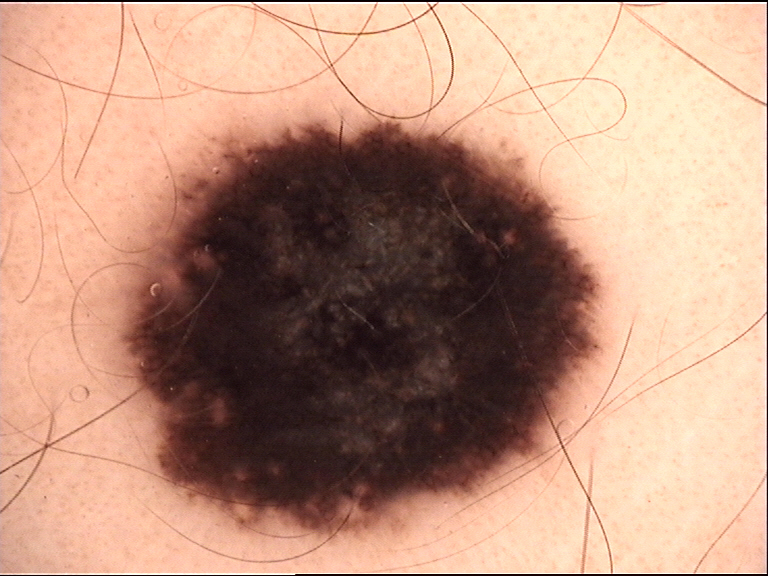<lesion>
<diagnosis>
<name>melanoma</name>
<code>mel</code>
<malignancy>malignant</malignancy>
<super_class>melanocytic</super_class>
<confirmation>histopathology</confirmation>
</diagnosis>
</lesion>